The patient notes the lesion is raised or bumpy. Self-categorized by the patient as a rash. The lesion is associated with itching. The patient notes the condition has been present for less than one week. The affected area is the arm and head or neck. No associated systemic symptoms reported. This image was taken at a distance: 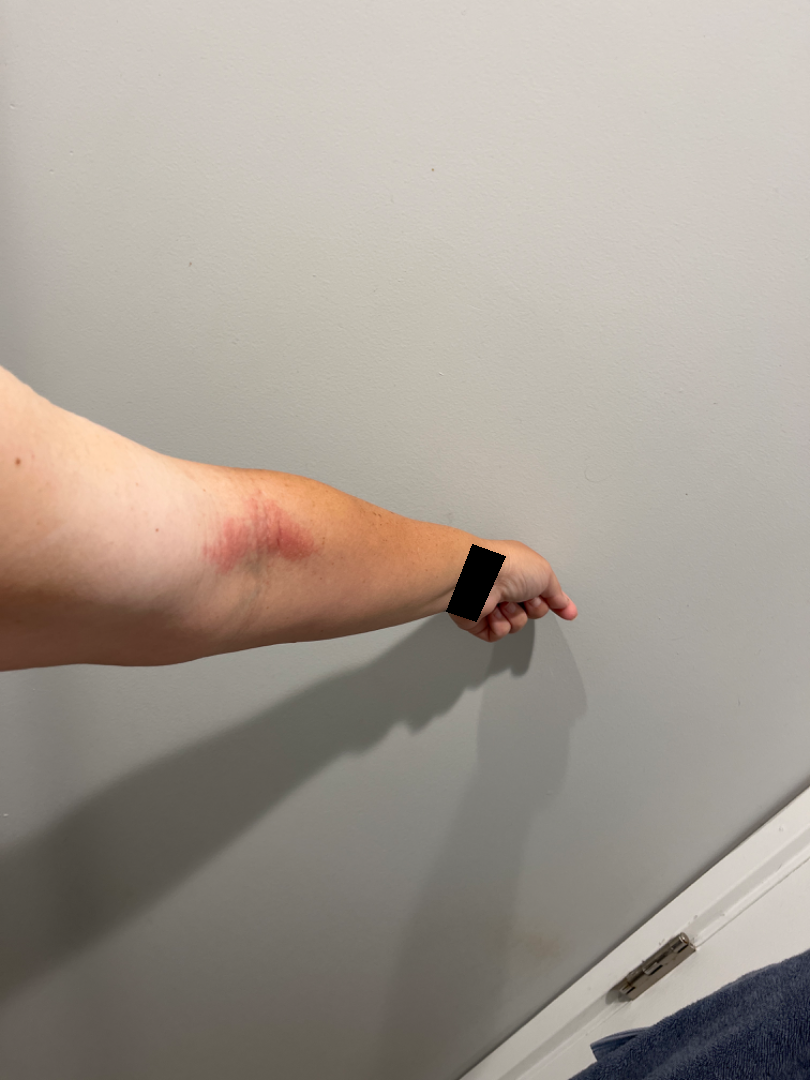Findings:
– dermatologist impression · in keeping with Eczema